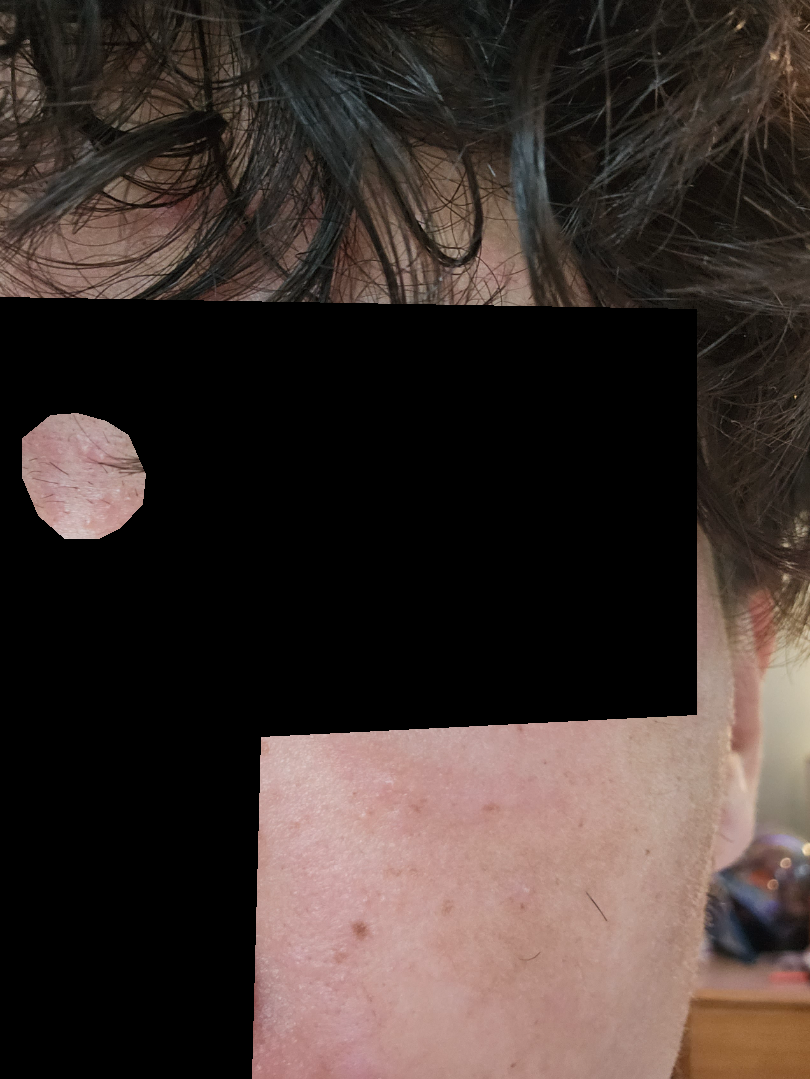  assessment: ungradable on photographic review
  shot_type: close-up